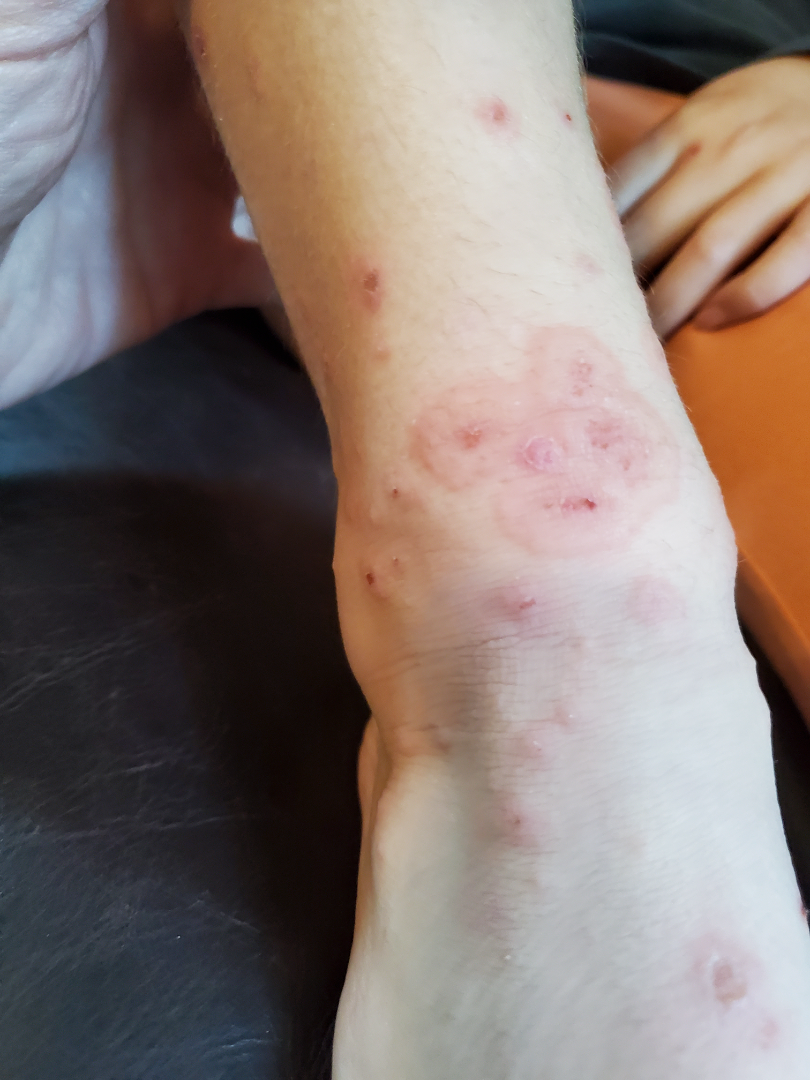Clinical context: The photograph is a close-up of the affected area. Assessment: A single dermatologist reviewed the case: consistent with Erythema multiforme.